The affected area is the arm · the contributor is 30–39, female · the photograph was taken at a distance — 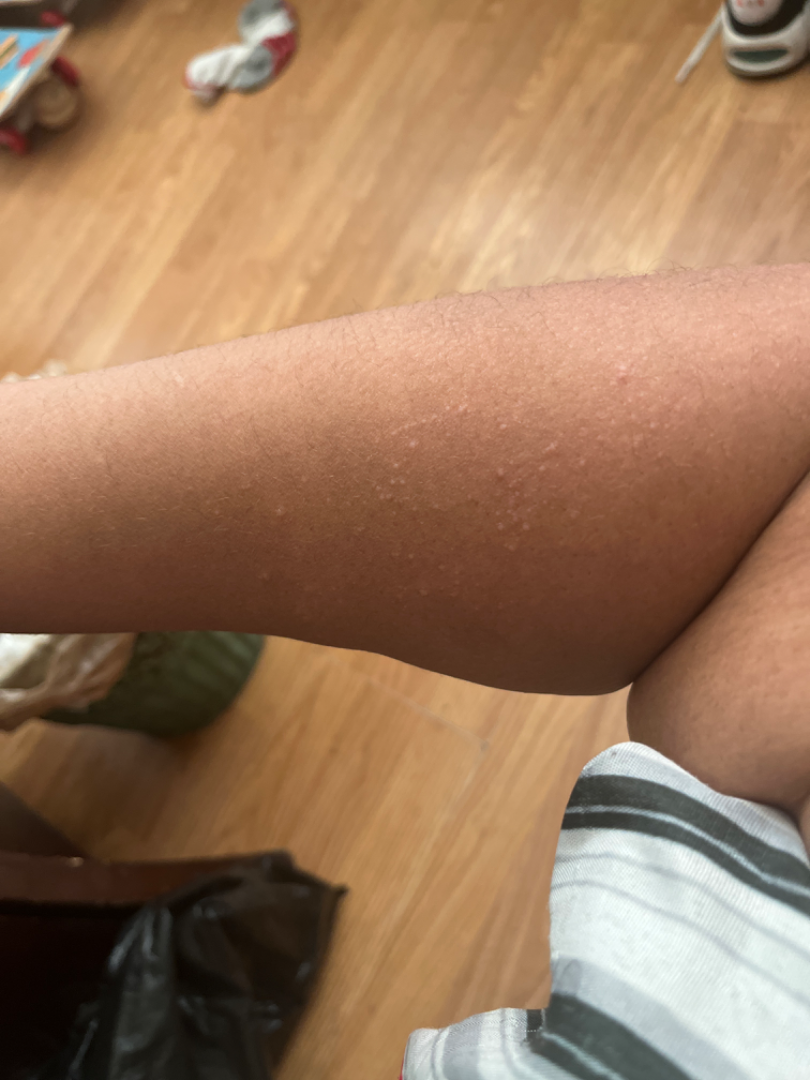Findings:
– symptoms: itching
– constitutional symptoms: none reported
– skin tone: Fitzpatrick phototype II; lay reviewers estimated Monk Skin Tone 3 or 5
– present for: one to four weeks
– texture: raised or bumpy
– dermatologist impression: most likely Eczema; with consideration of Lichen nitidus; lower on the differential is Keratosis pilaris